This is a dermoscopic photograph of a skin lesion.
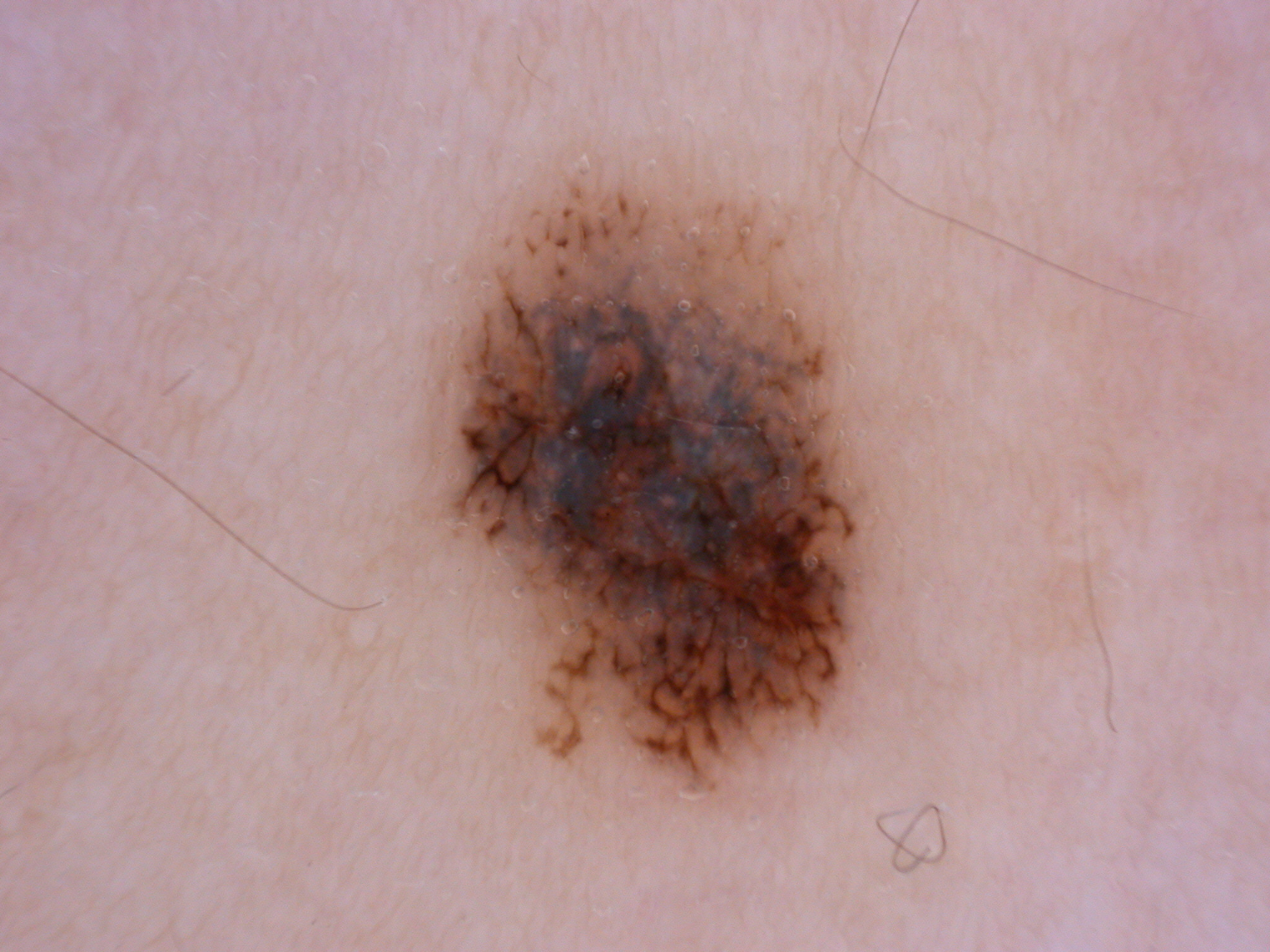dermoscopic pattern = pigment network and streaks; absent: globules, milia-like cysts, and negative network | lesion extent = ~17% of the field | location = 410, 181, 882, 791 | impression = a melanocytic nevus.